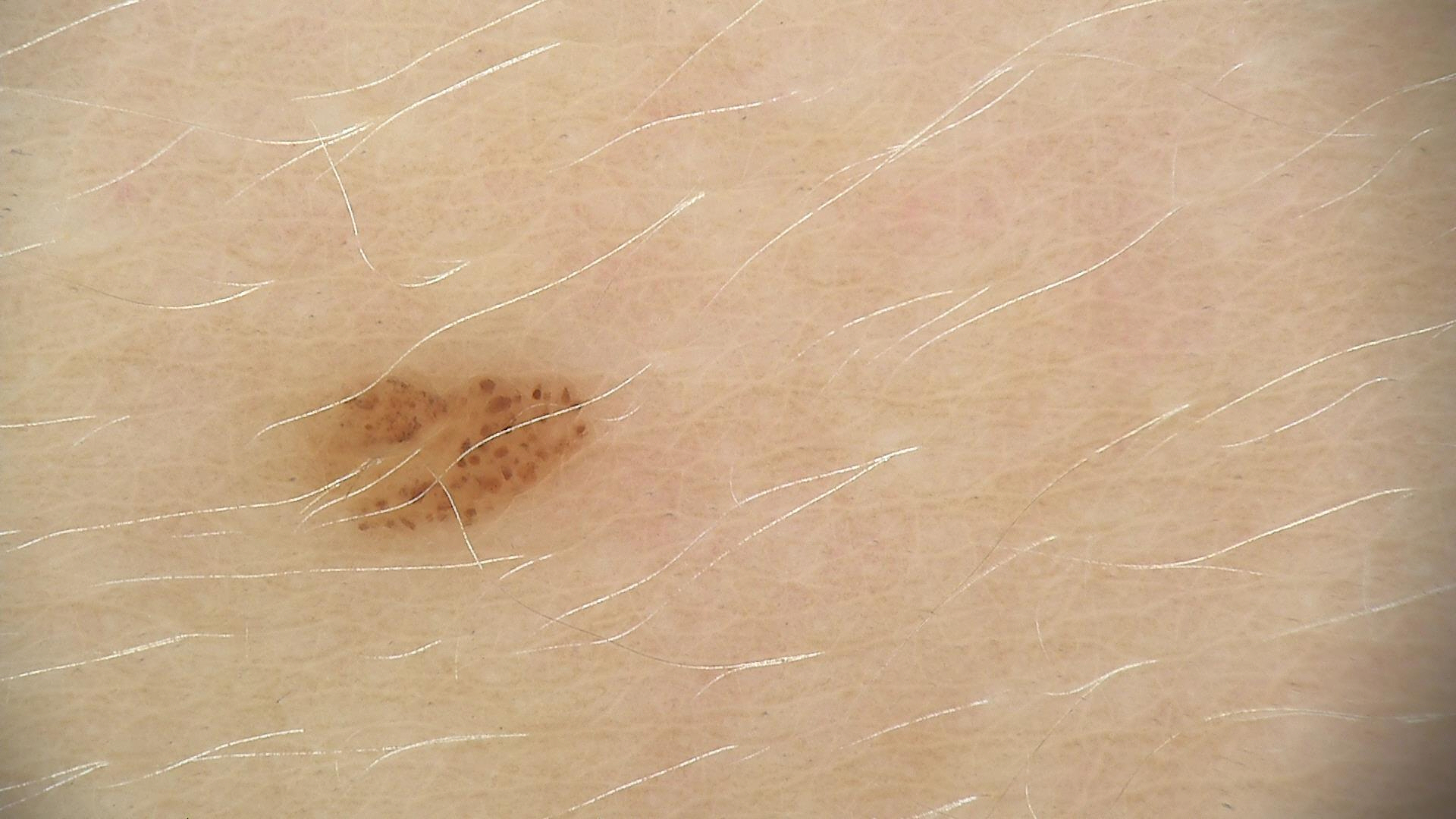{
  "image": "dermoscopy",
  "diagnosis": {
    "name": "dysplastic junctional nevus",
    "code": "jd",
    "malignancy": "benign",
    "super_class": "melanocytic",
    "confirmation": "expert consensus"
  }
}